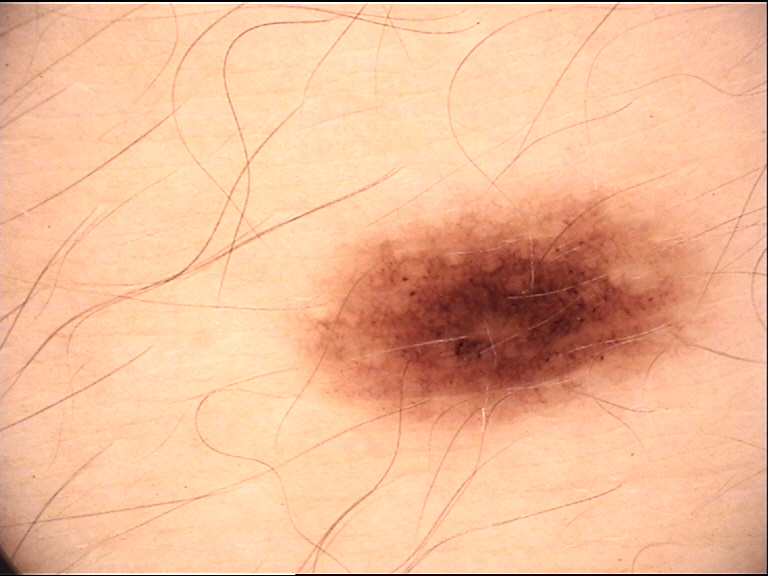modality=dermatoscopy | label=dysplastic junctional nevus (expert consensus).